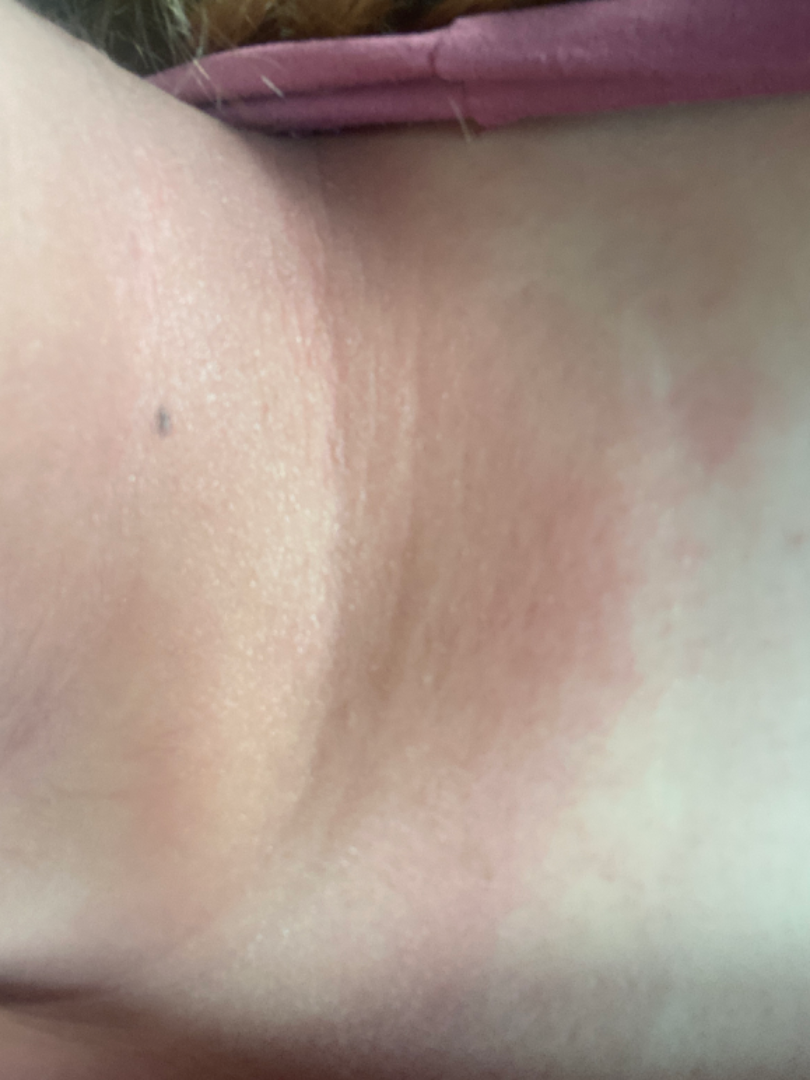assessment = the leading impression is Intertrigo; also raised was Allergic Contact Dermatitis; less likely is Irritant Contact Dermatitis; less probable is Photodermatitis; lower on the differential is Cellulitis; a more distant consideration is Hypersensitivity.